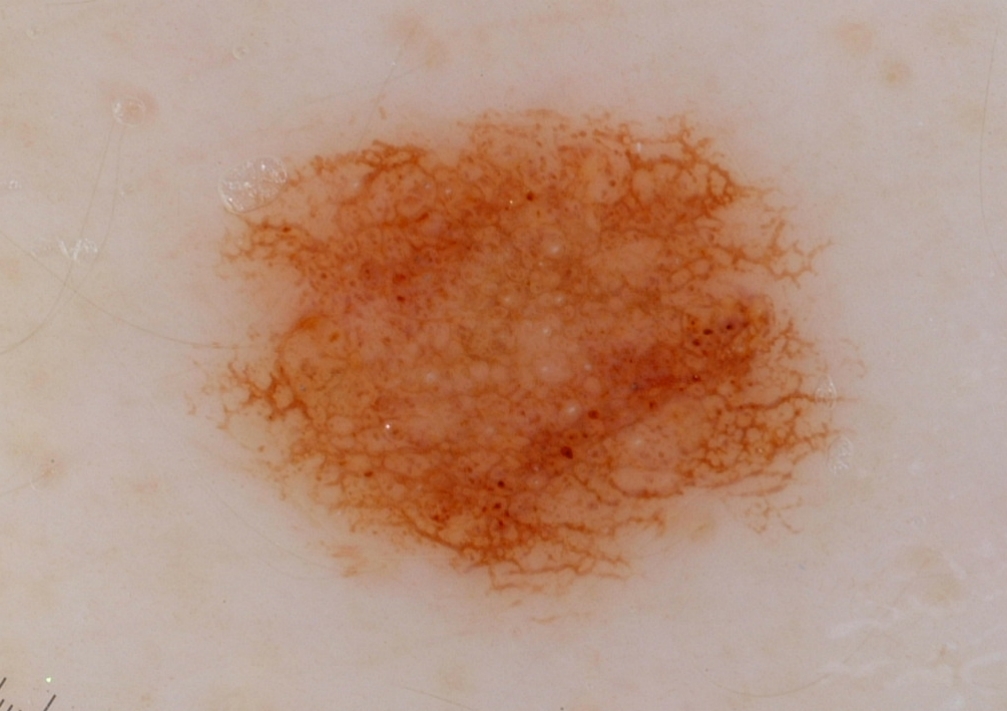Image and clinical context:
A skin lesion imaged with a dermatoscope. The dermoscopic pattern shows globules, pigment network, and milia-like cysts. The lesion occupies roughly 36% of the field. With coordinates (x1, y1, x2, y2), the lesion spans 193 90 849 624.
Conclusion:
The clinical diagnosis was a melanocytic nevus.